A male patient age 89; referred with a clinical suspicion of basal cell carcinoma; a skin lesion imaged with a dermatoscope.
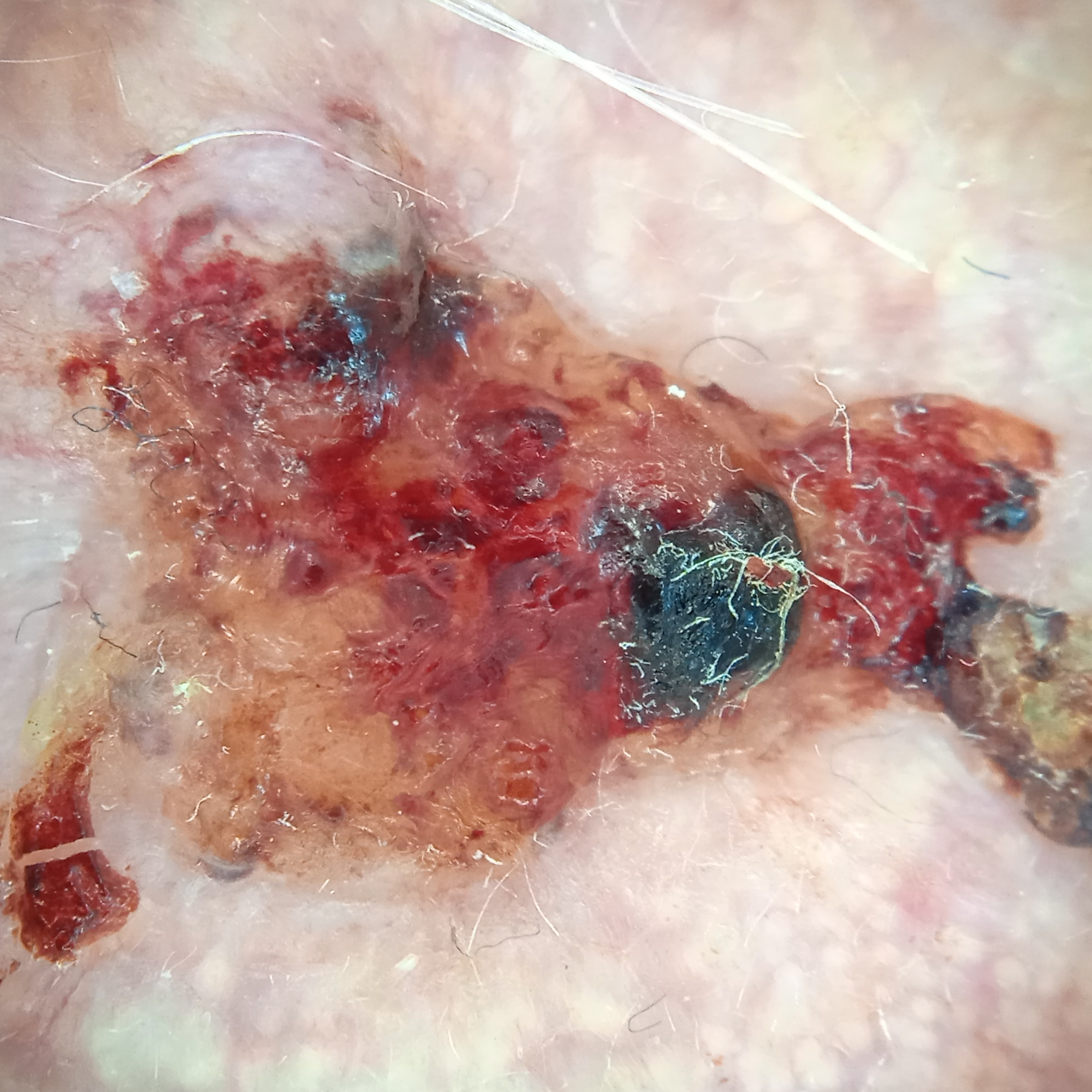Findings:
- site · the face
- diameter · 14.9 mm
- diagnosis · basal cell carcinoma (biopsy-proven)